Close-up view, located on the top or side of the foot, self-categorized by the patient as a rash, the condition has been present for less than one week, reported lesion symptoms include darkening.
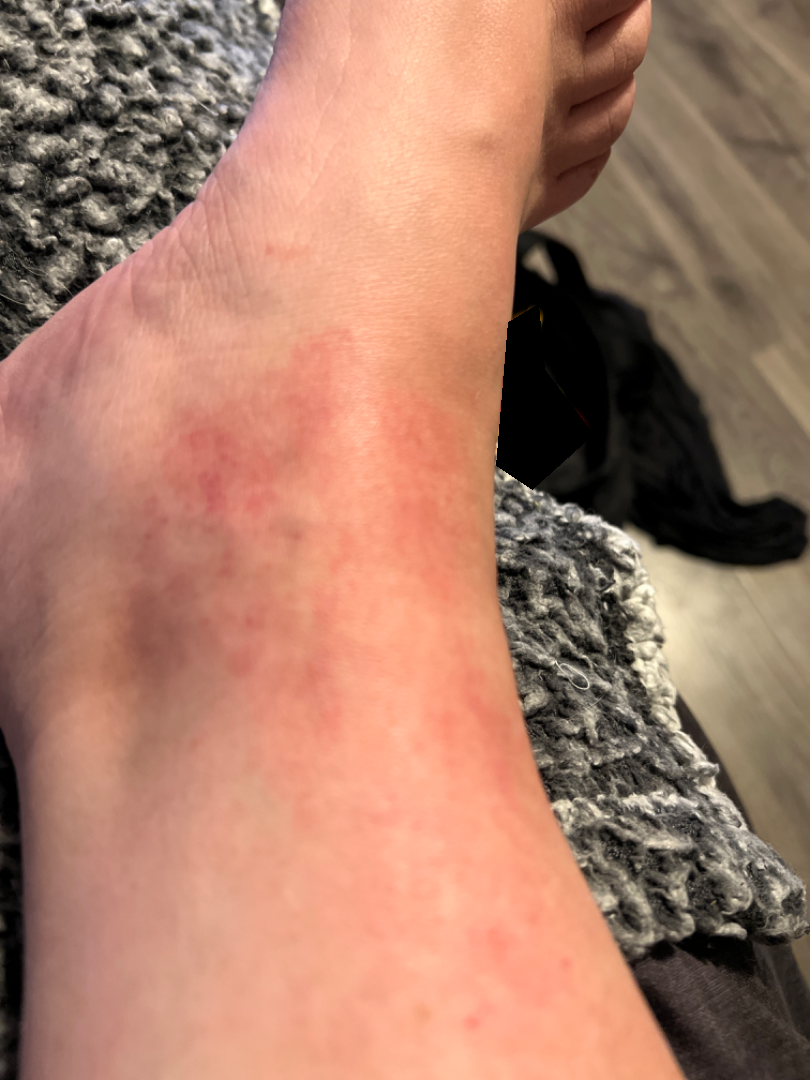The image was not sufficient for the reviewer to characterize the skin condition.